A dermoscopic close-up of a skin lesion · a female subject aged around 45: 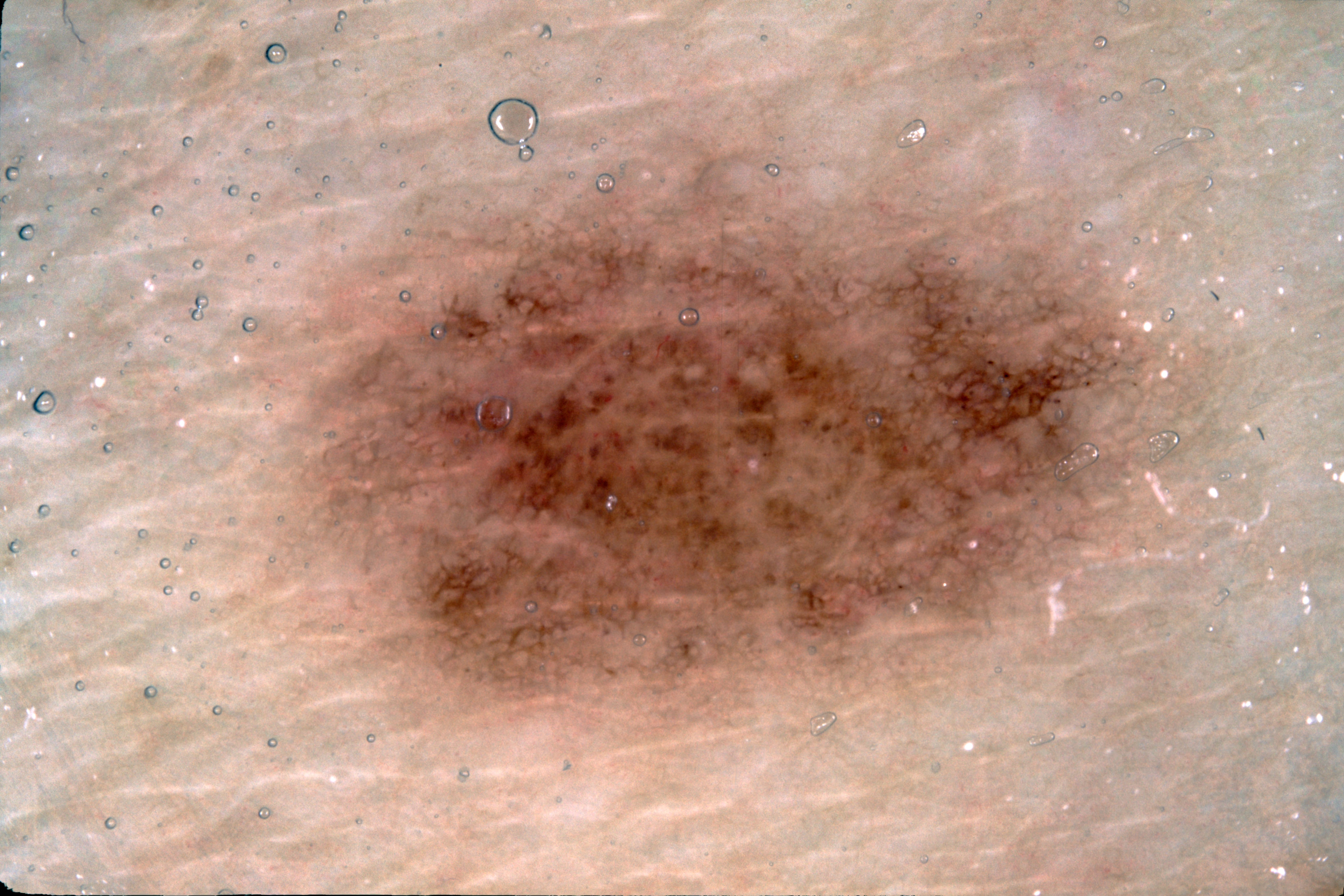The dermoscopic pattern shows pigment network. As (left, top, right, bottom), lesion location: bbox=[281, 118, 1224, 714]. Diagnosed as a melanocytic nevus, a benign skin lesion.